A dermoscopic image of a skin lesion.
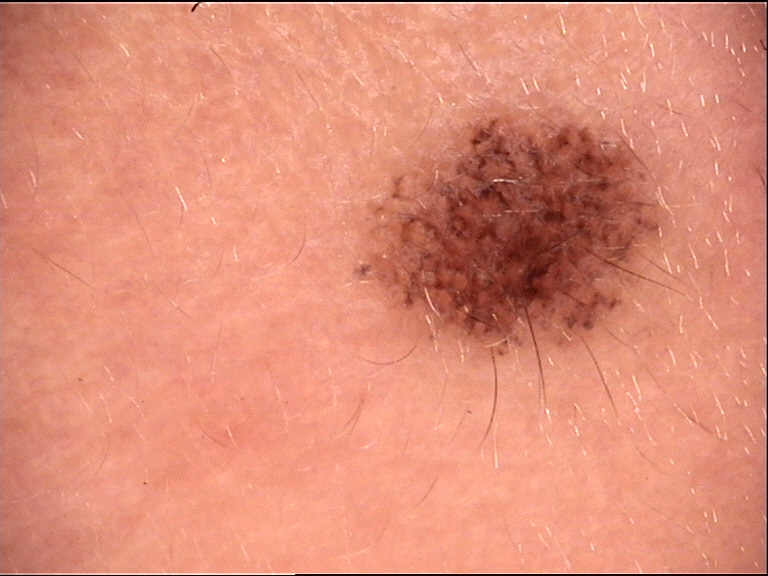Conclusion:
Classified as a Miescher nevus.